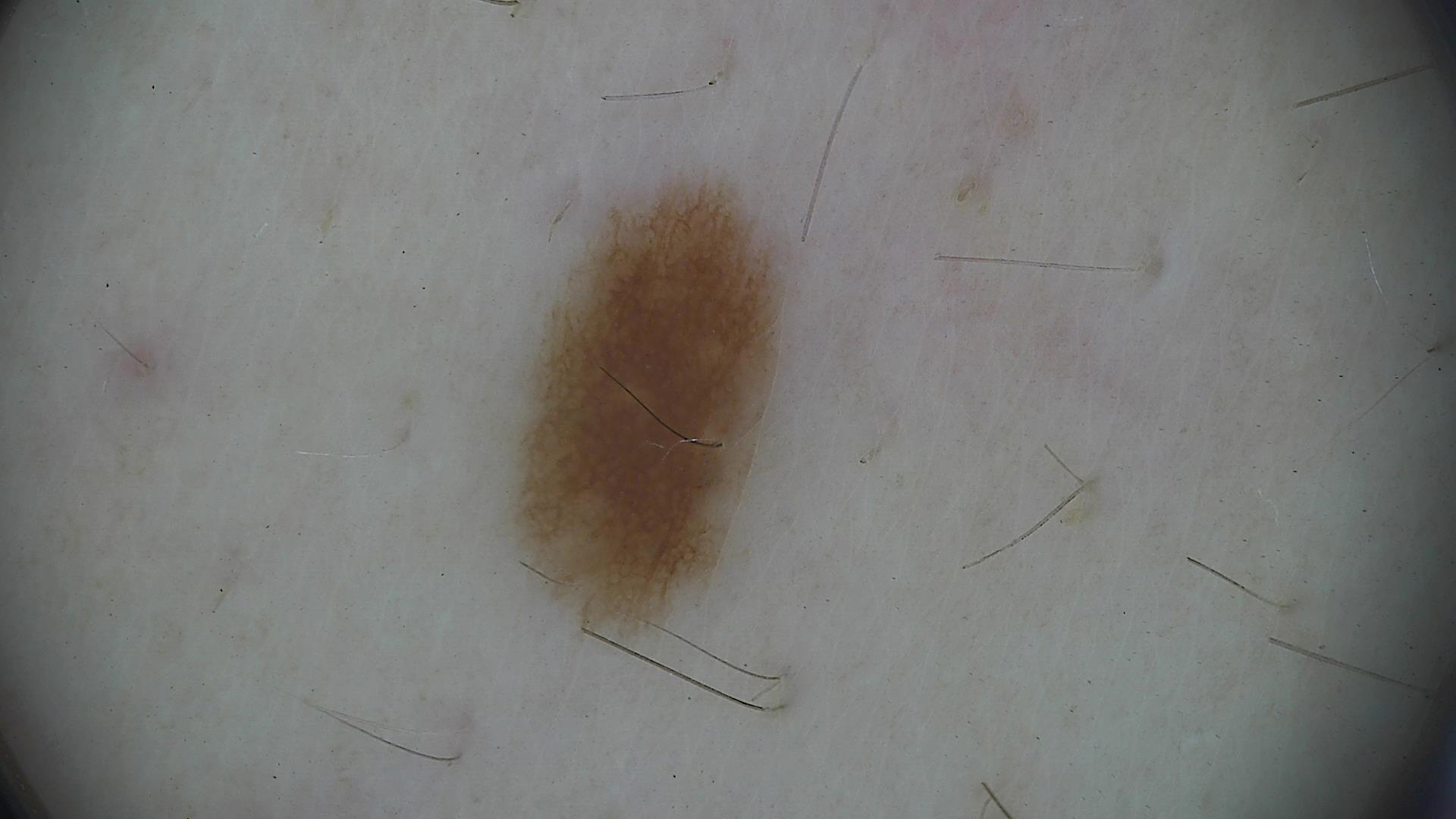diagnostic label — dysplastic junctional nevus (expert consensus)